A dermoscopy image of a single skin lesion.
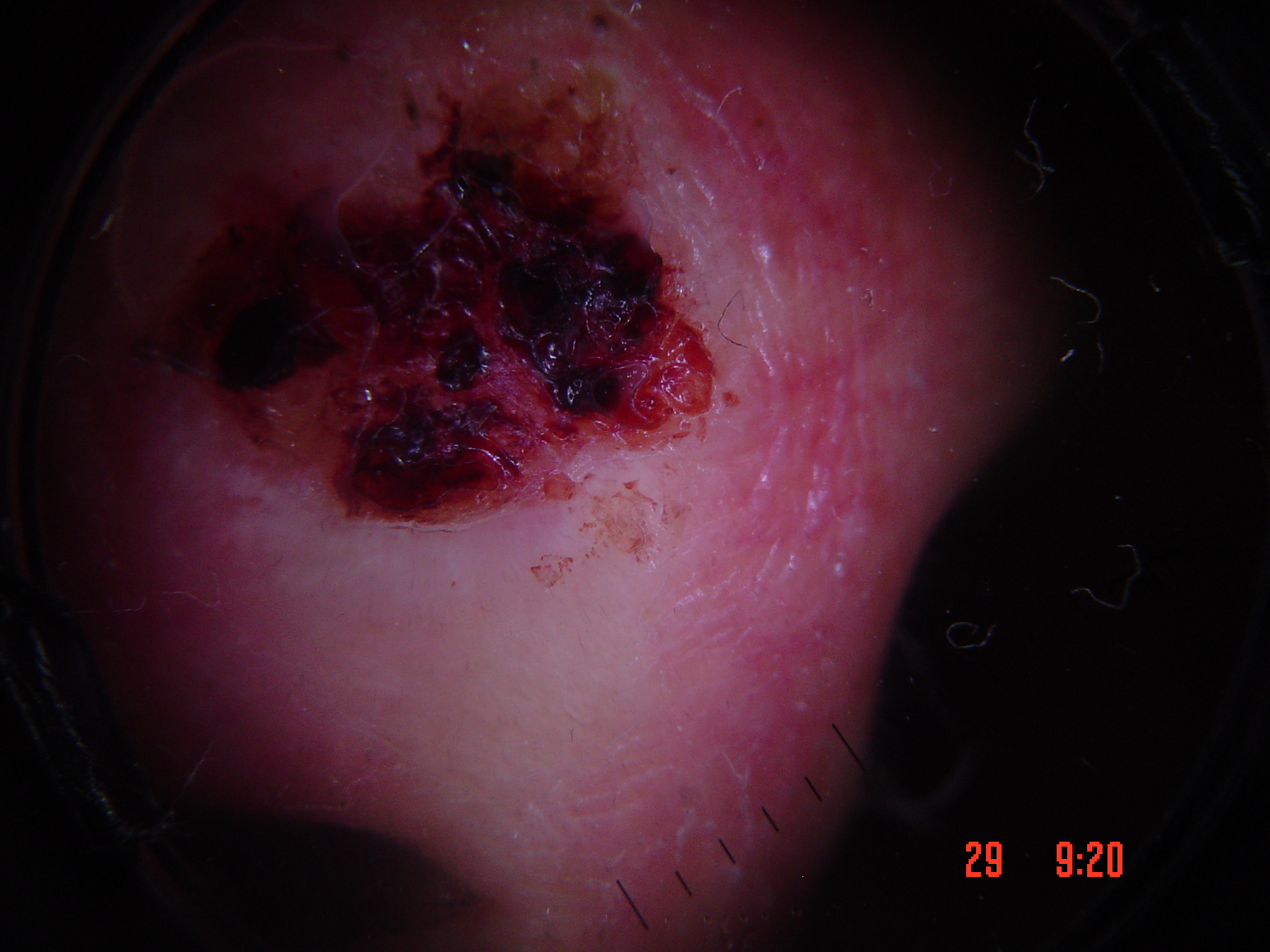diagnosis: squamous cell carcinoma (biopsy-proven)